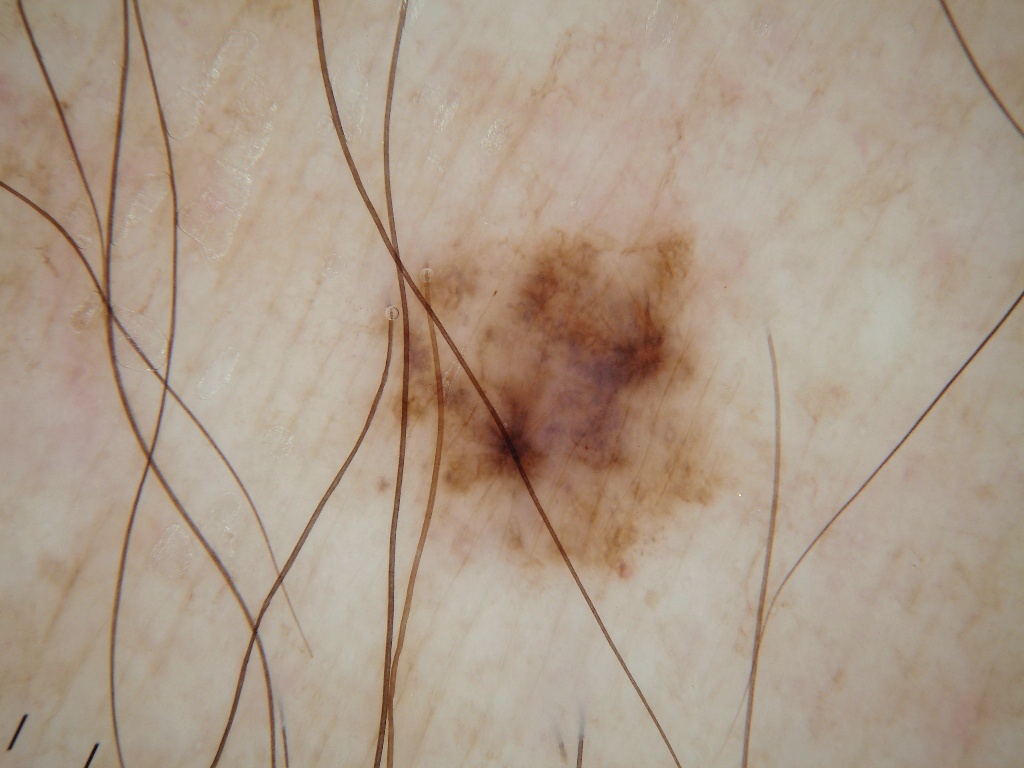A dermatoscopic image of a skin lesion.
The patient is a male roughly 60 years of age.
With coordinates (x1, y1, x2, y2), the lesion occupies the region [349,209,724,604].
The dermoscopic pattern shows globules, streaks, and pigment network; no negative network or milia-like cysts.
The lesion was assessed as a melanocytic nevus, a benign lesion.